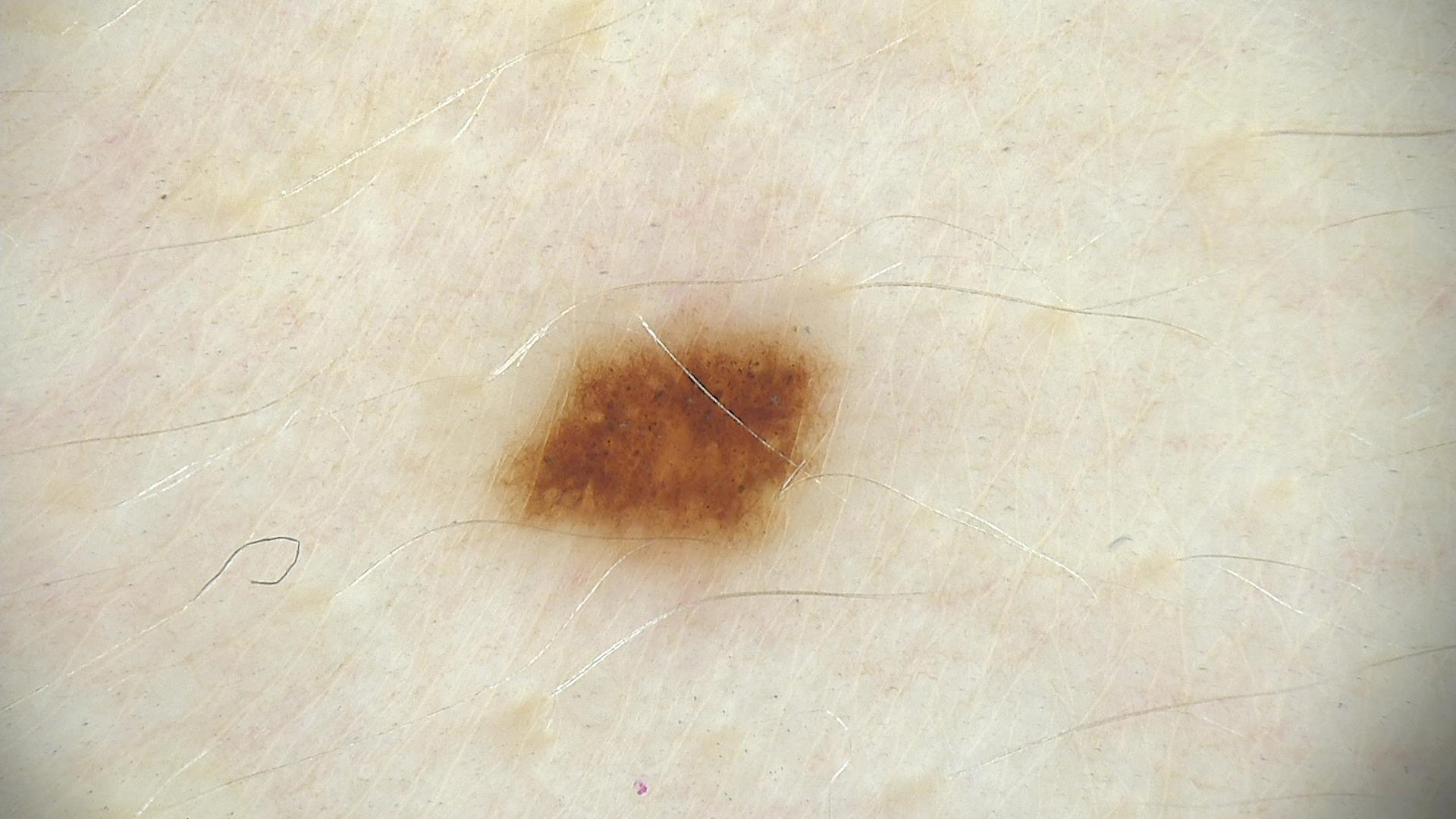  image: dermoscopy
  diagnosis:
    name: dysplastic junctional nevus
    code: jd
    malignancy: benign
    super_class: melanocytic
    confirmation: expert consensus